A dermoscopy image of a single skin lesion: 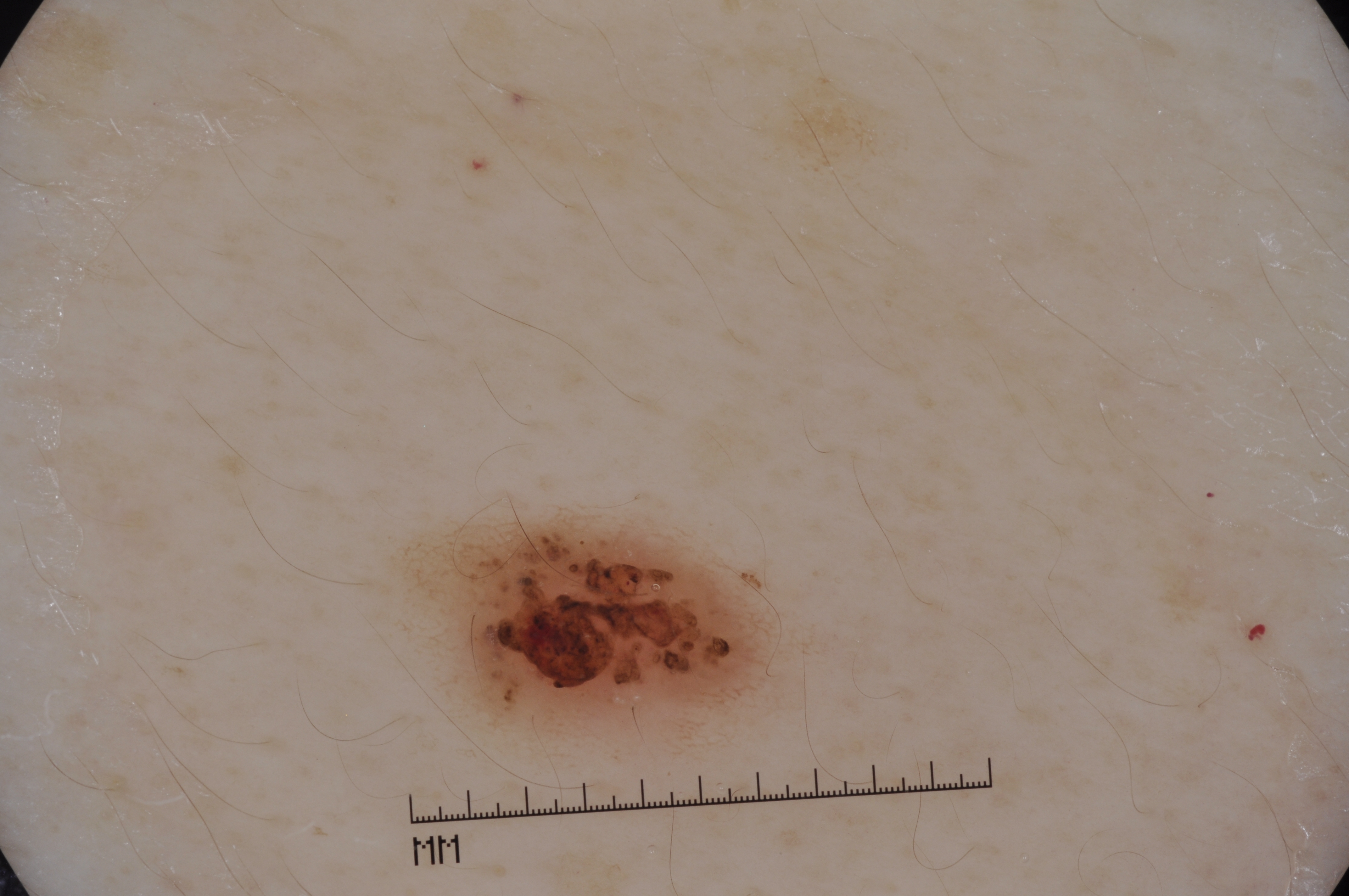Image and clinical context: The lesion is located at [411, 518, 780, 735]. Conclusion: The lesion was assessed as a melanocytic nevus, a benign skin lesion.